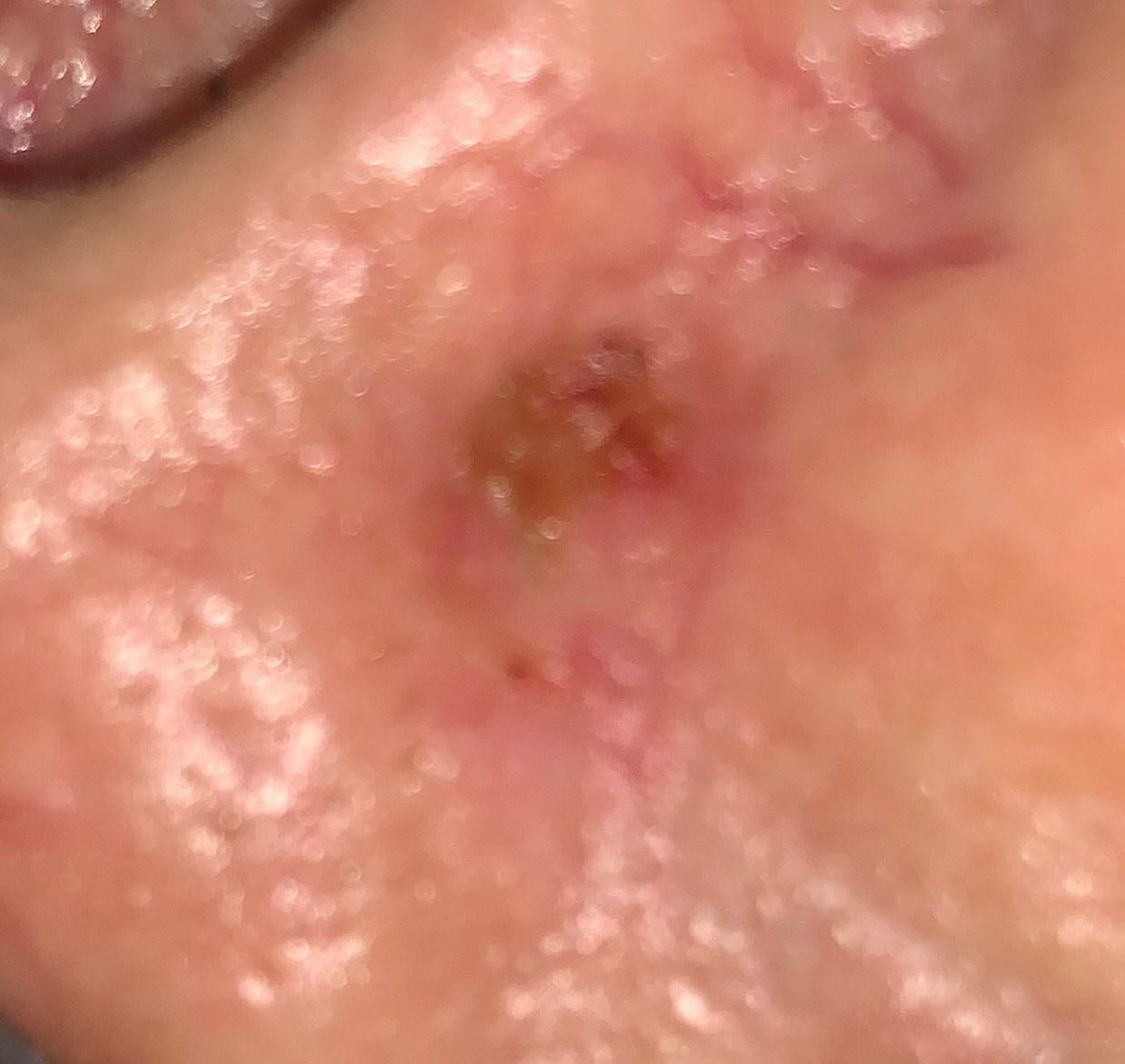A male subject aged around 60.
A wide-field clinical photograph of a skin lesion.
The patient is FST III.
Located on the head or neck.
Biopsy-confirmed as a malignant lesion — a basal cell carcinoma.